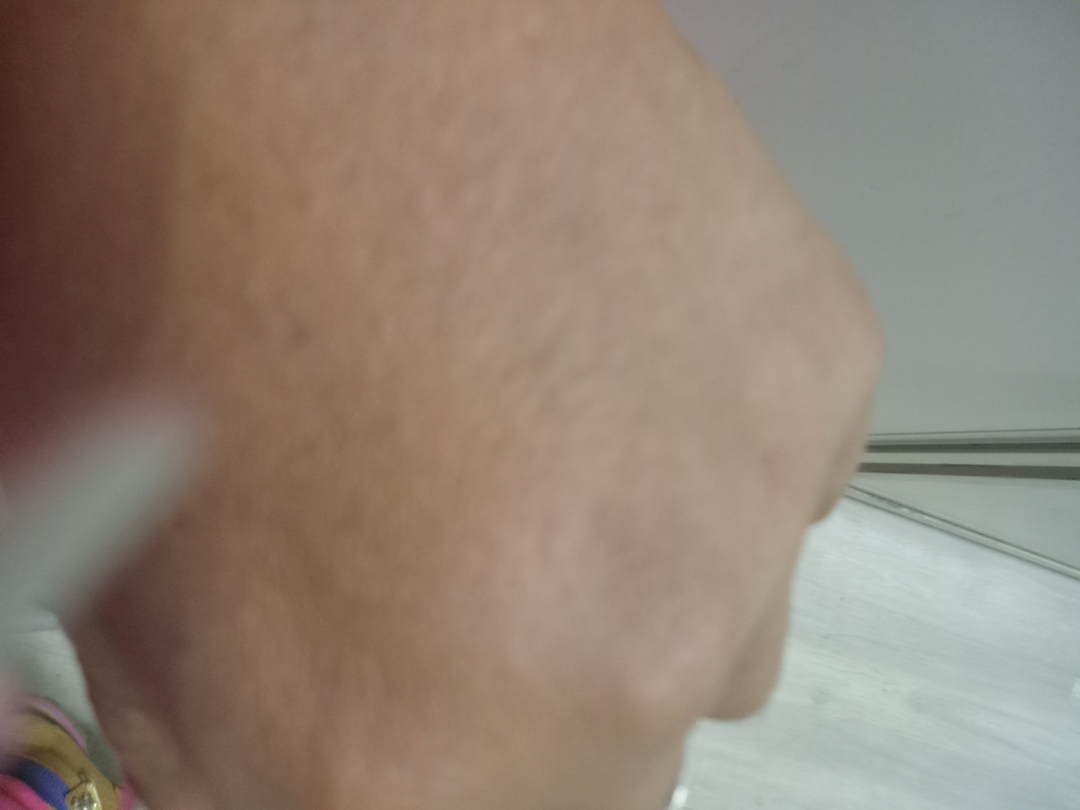The image was not sufficient for the reviewer to characterize the skin condition. A close-up photograph.